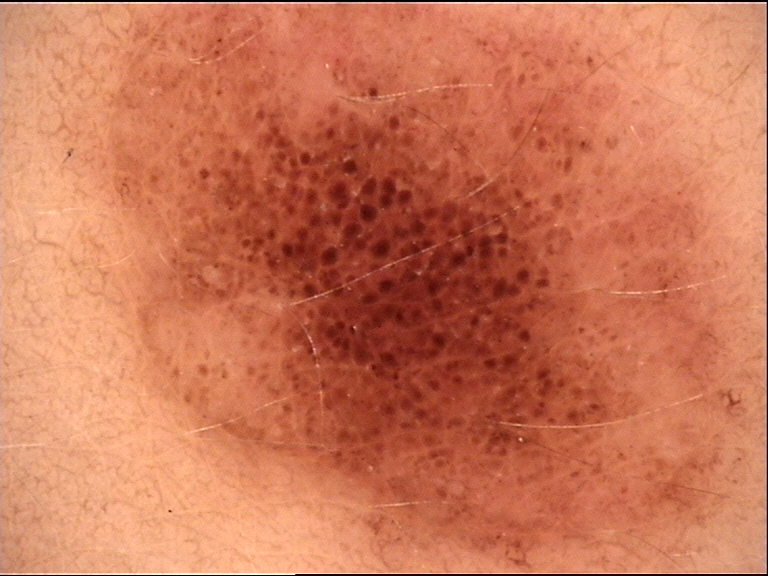Q: What was the diagnostic impression?
A: compound nevus (expert consensus)